A dermoscopic close-up of a skin lesion:
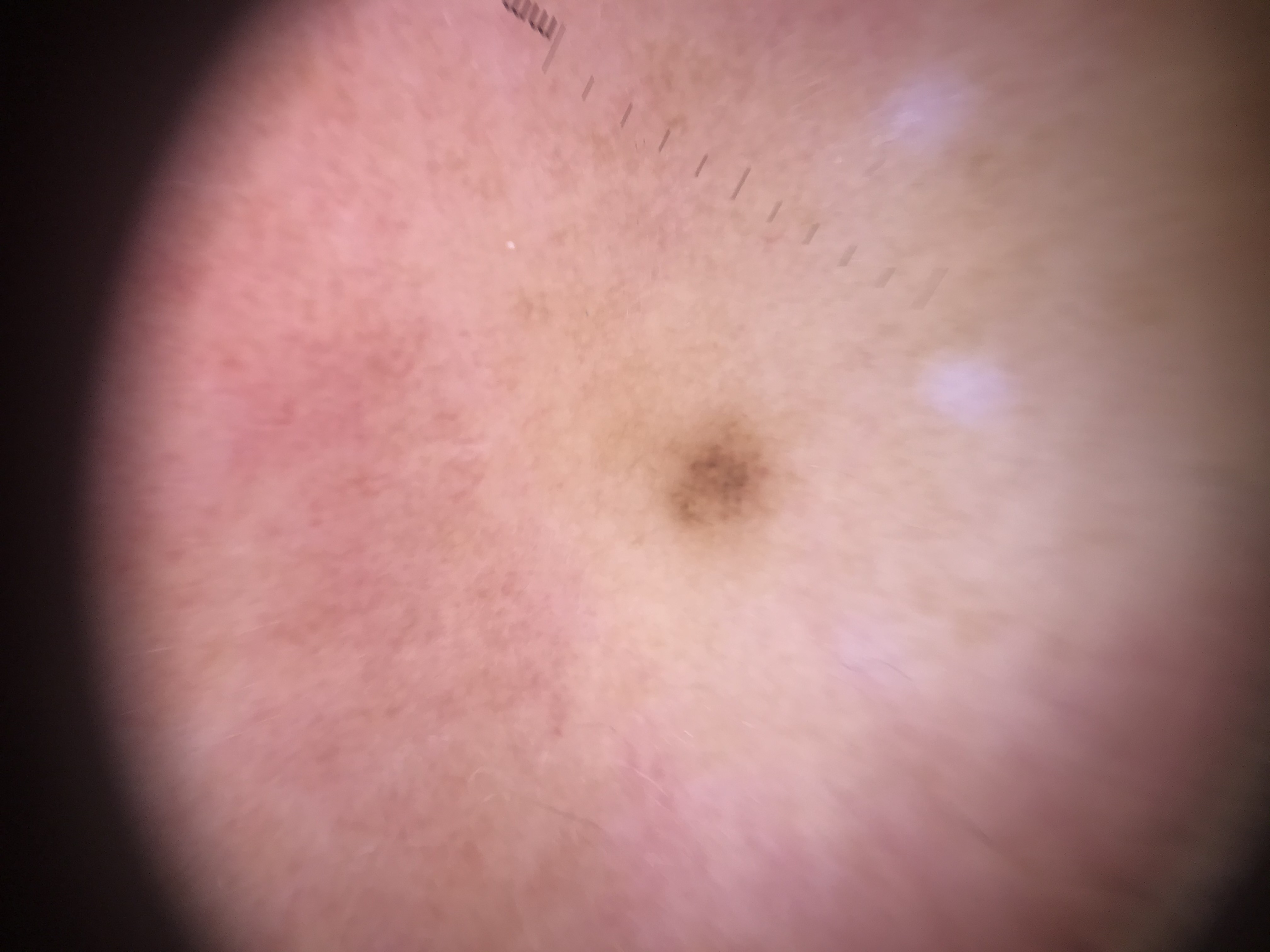lesion type — banal
class — junctional nevus (expert consensus)